The affected area is the arm. Close-up view:
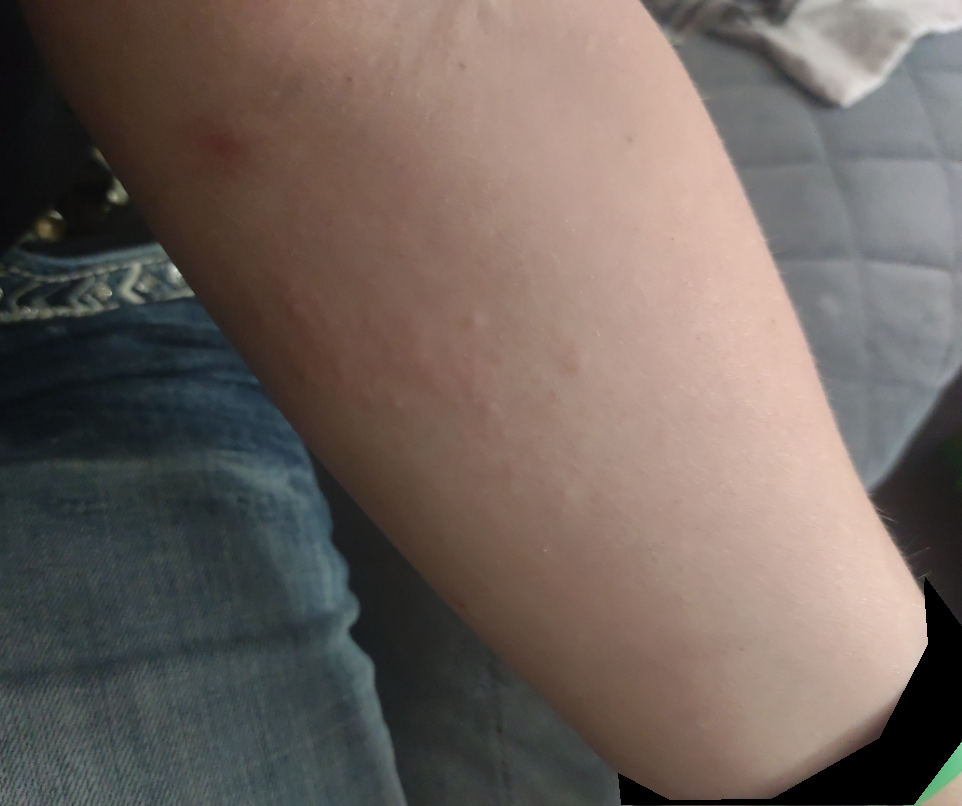Review: The skin findings could not be characterized from the image.